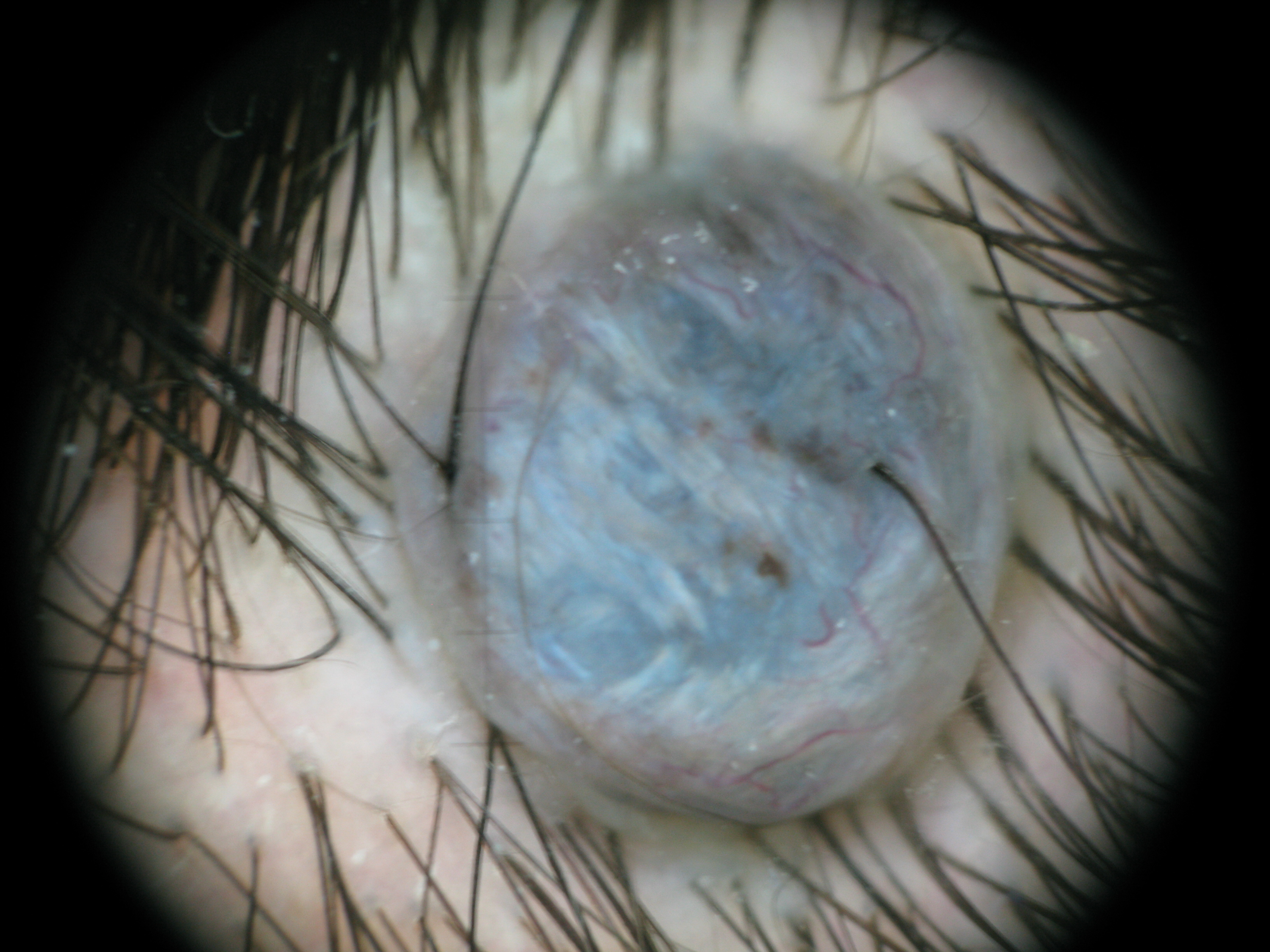| key | value |
|---|---|
| modality | dermatoscopy |
| classification | banal, dermal |
| diagnostic label | blue nevus (expert consensus) |